Dermoscopy of a skin lesion: 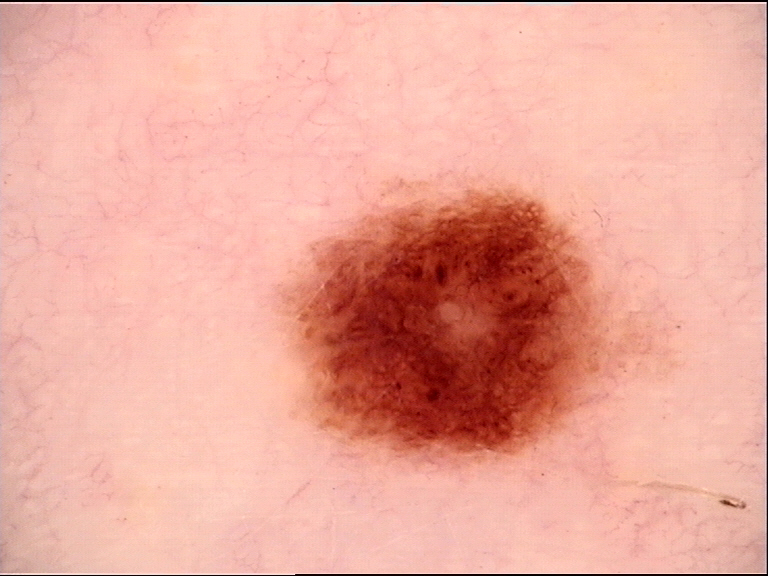The diagnostic label was a benign lesion — a dysplastic junctional nevus.